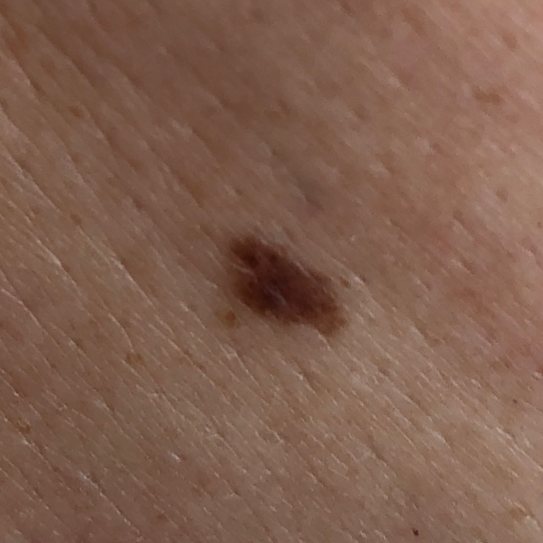risk factors: alcohol use, prior malignancy (patient or family), pesticide exposure; patient: female, age 59; image: smartphone clinical photo; diameter: 4x3 mm; reported symptoms: no bleeding, no itching; pathology: nevus (biopsy-proven).